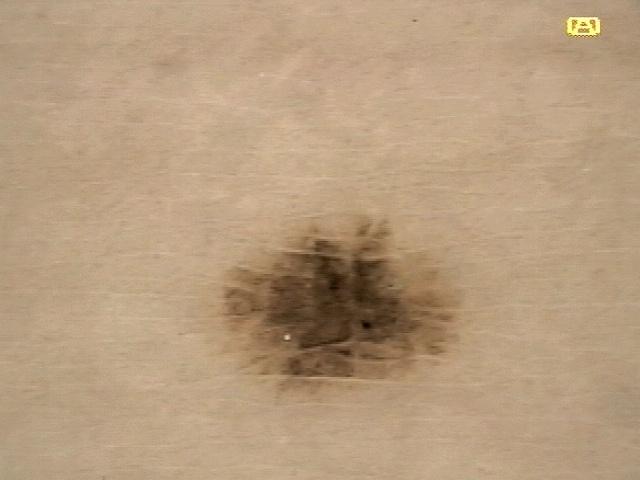Case:
– skin phototype: II
– patient: female, aged approximately 20
– diagnosis: Nevus (clinical impression)